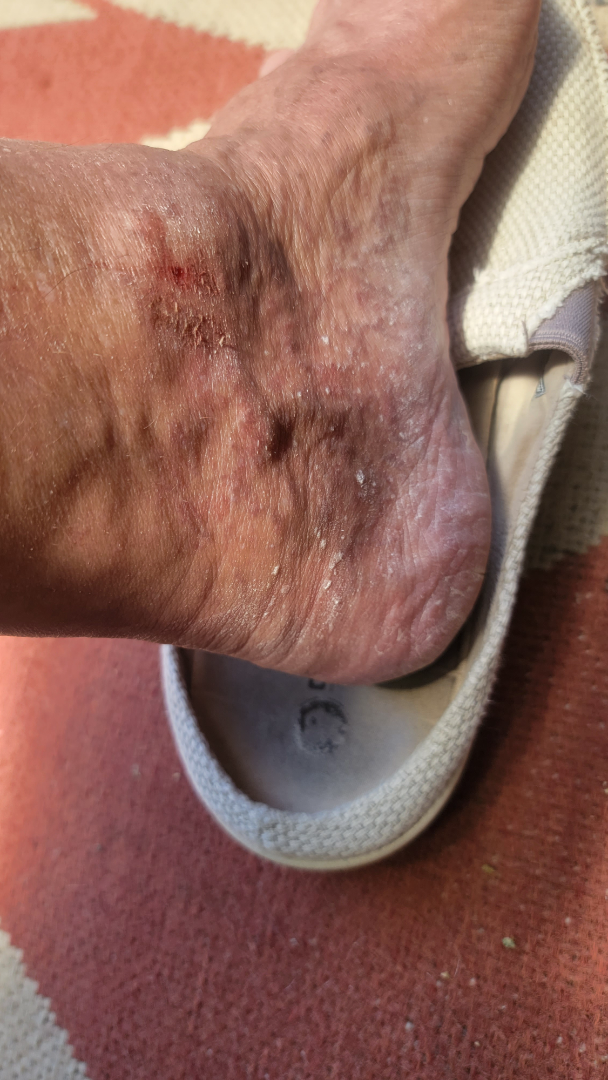The condition has been present for one to four weeks. The patient notes itching, burning, bothersome appearance and bleeding. The lesion is described as raised or bumpy and rough or flaky. The photograph is a close-up of the affected area. The affected area is the top or side of the foot. Male contributor, age 70–79.